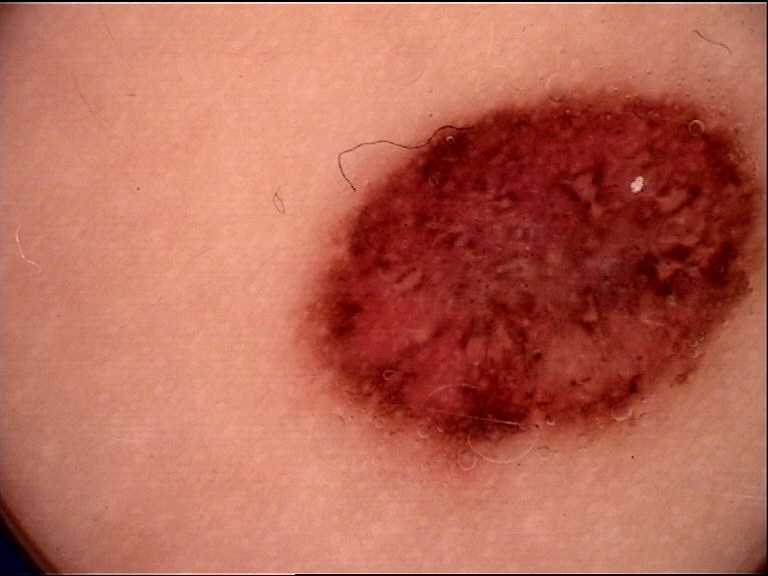A dermoscopic image of a skin lesion. This is a banal lesion. Labeled as a congenital compound nevus.